The photograph was taken at a distance: 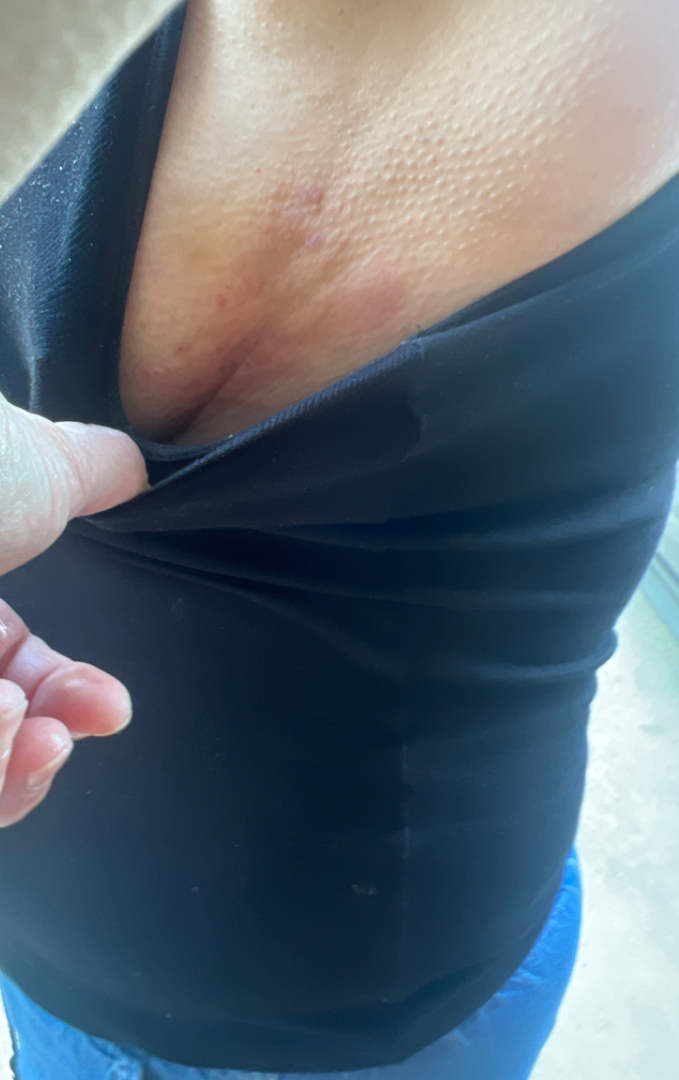Findings: The dermatologist could not determine a likely condition from the photograph alone. Background: Symptoms reported: itching, enlargement, darkening and bothersome appearance. Lay graders estimated Monk skin tone scale 5 (US pool) or 2 (India pool). Texture is reported as raised or bumpy. Self-categorized by the patient as a rash.